The lesion involves the leg; symptoms reported: itching; the patient indicates the condition has been present for about one day; this image was taken at an angle; texture is reported as raised or bumpy; the patient is female: 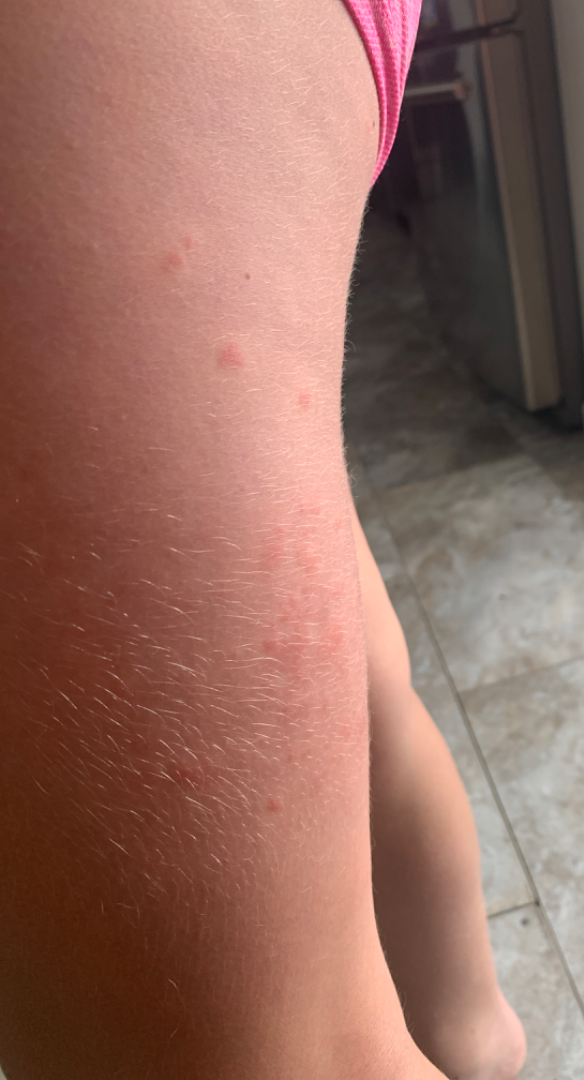The reviewing panel's impression was: most likely Insect Bite; possibly Urticaria; less probable is Allergic Contact Dermatitis.